A male subject roughly 40 years of age; the patient was assessed as Fitzpatrick skin type III.
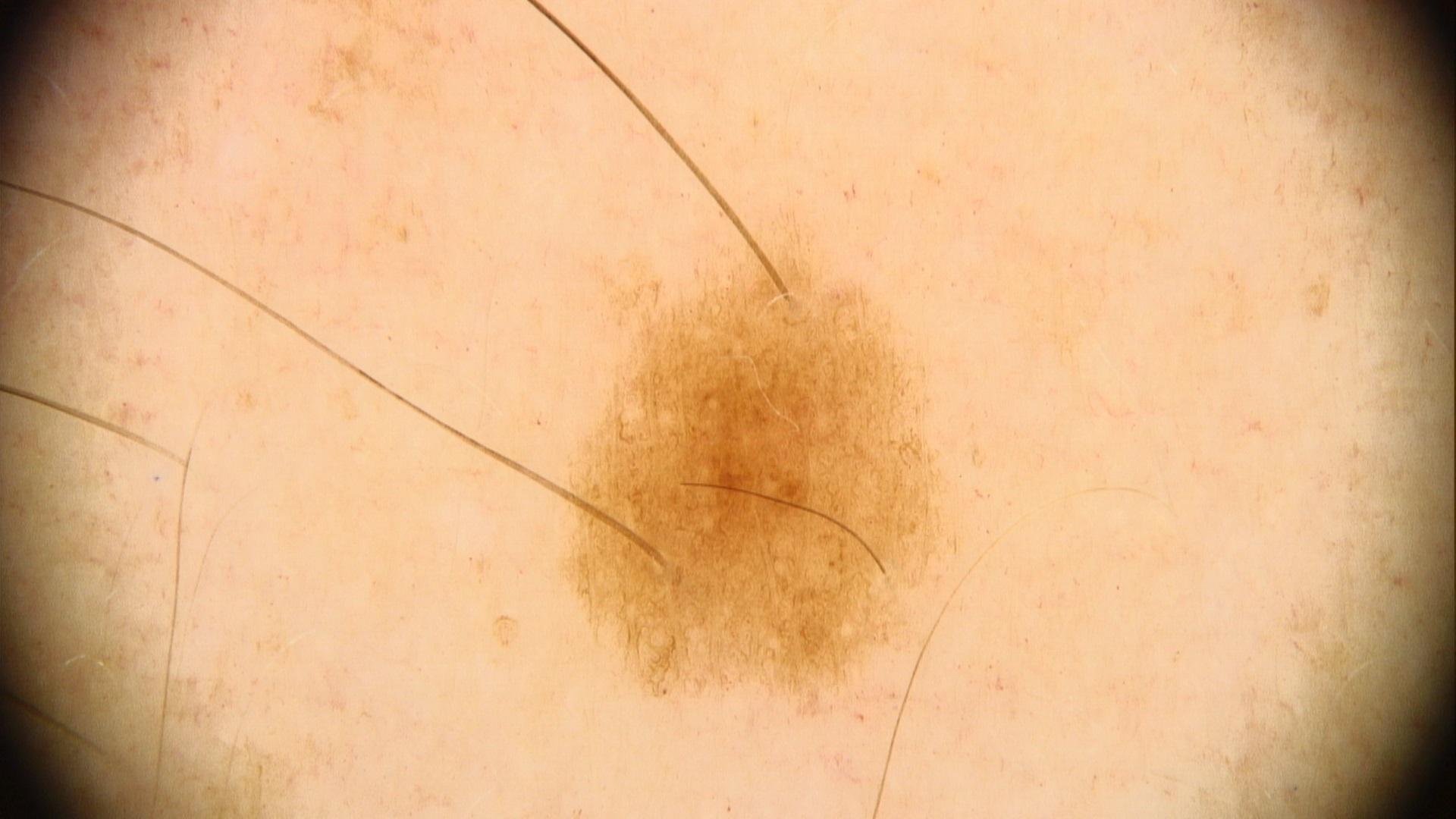The clinical impression was a benign lesion — a nevus.